A female patient age 34. A clinical photograph showing a skin lesion — 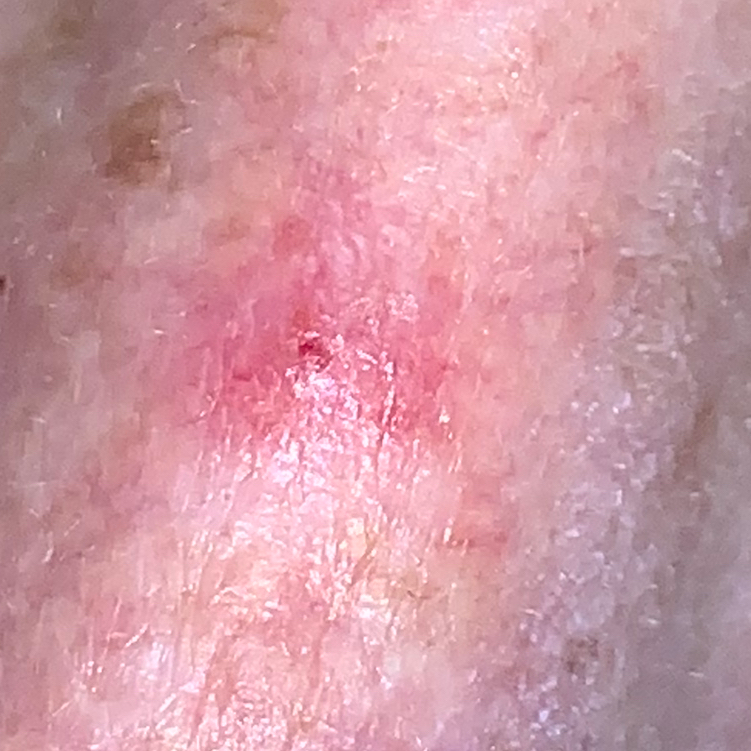The lesion was found on the nose. The biopsy diagnosis was a basal cell carcinoma.